The head or neck is involved. The patient considered this a rash. This is a close-up image. The lesion is associated with bothersome appearance and itching. No constitutional symptoms were reported. The lesion is described as raised or bumpy. Female patient, age 18–29. FST IV; human graders estimated Monk Skin Tone 3 or 5 (two reviewer pools disagreed). Reported duration is less than one week:
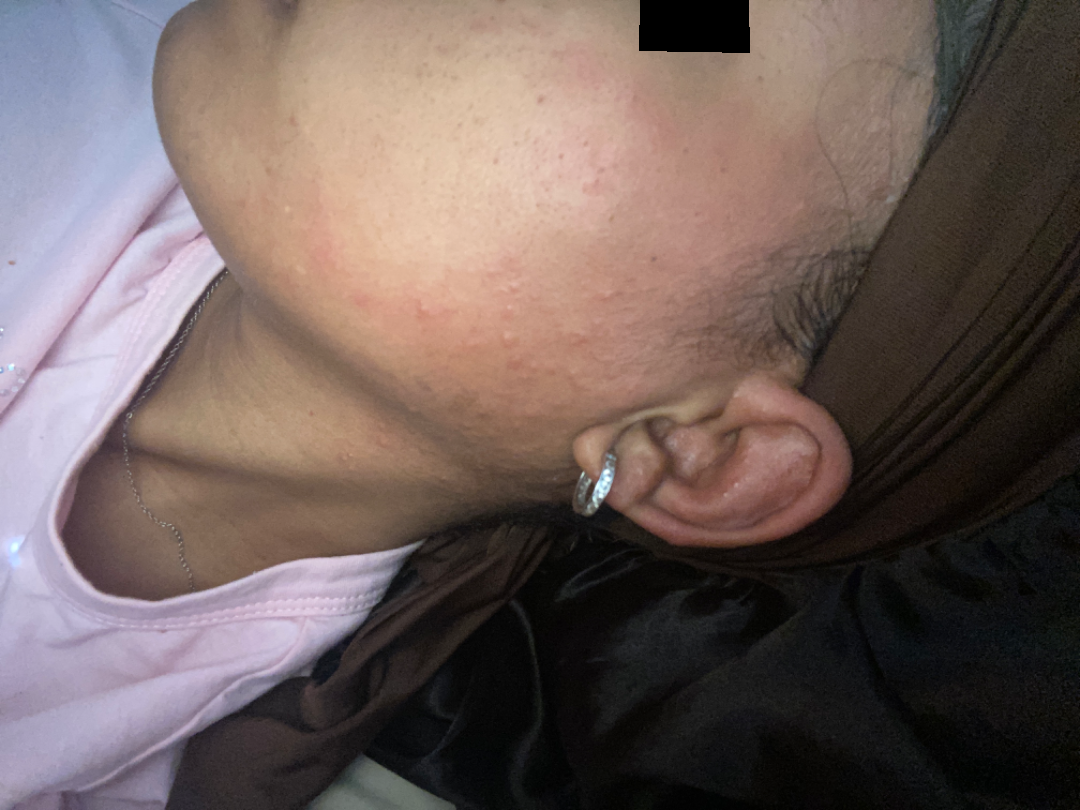On remote dermatologist review: Acne (weight 0.41); Rosacea (weight 0.41); Comedone (weight 0.18).